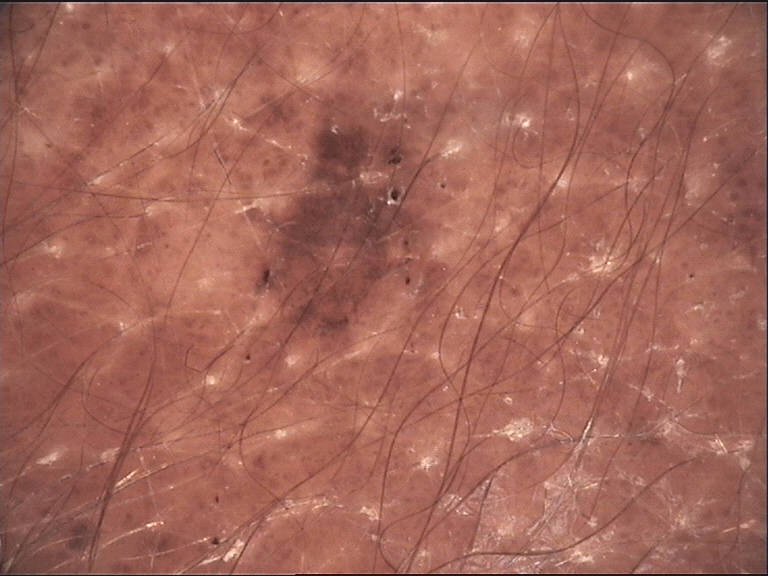  image: dermoscopy
  diagnosis:
    name: congenital compound nevus
    code: ccb
    malignancy: benign
    super_class: melanocytic
    confirmation: expert consensus